The patient describes having numerous moles · the patient says their skin tans without first burning · a female patient aged 78 · a skin lesion imaged with a dermatoscope · the patient reports no prior organ transplant · acquired for a research image collection, with no referral diagnosis: 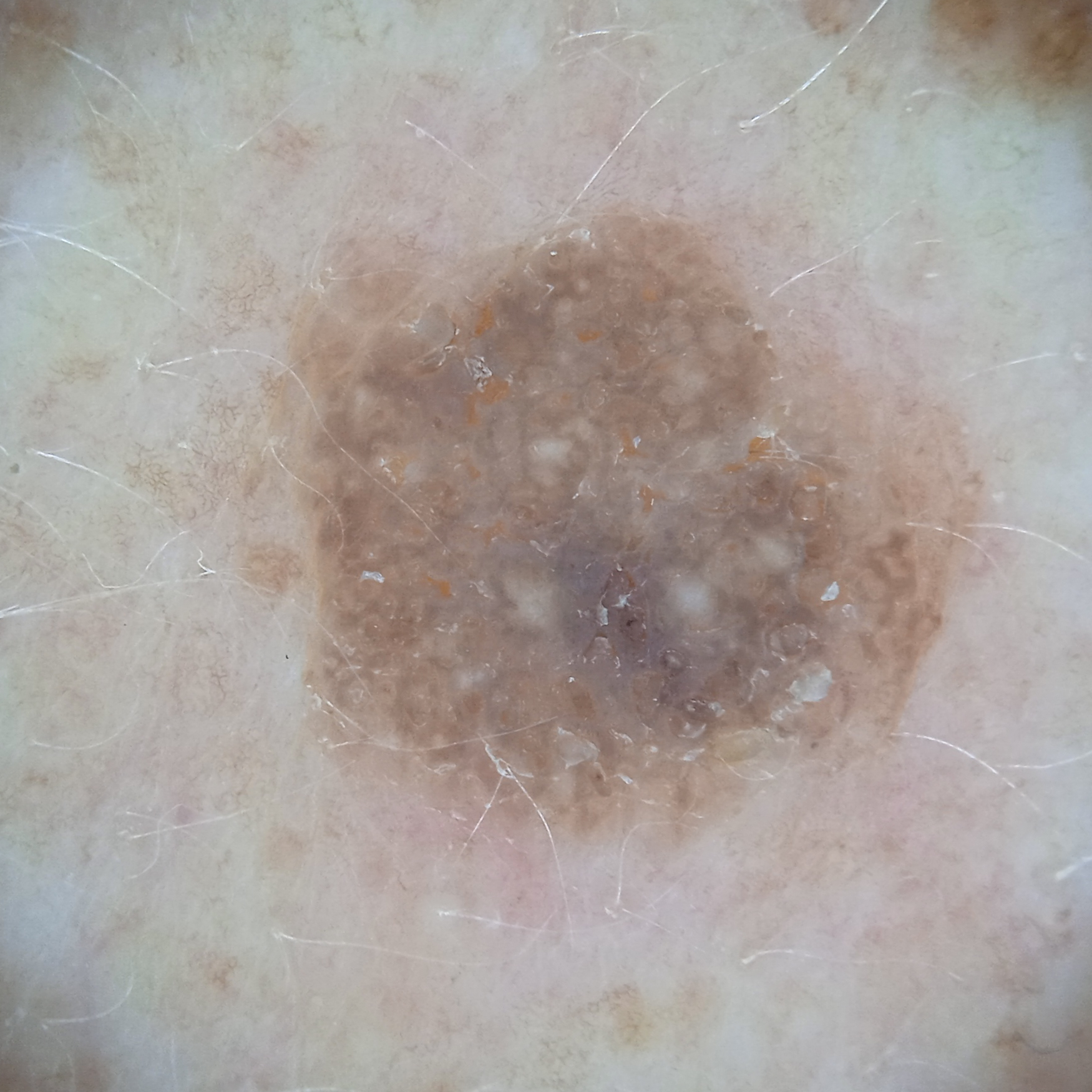location: the back
diameter: 7.3 mm
diagnostic label: seborrheic keratosis (dermatologist consensus)